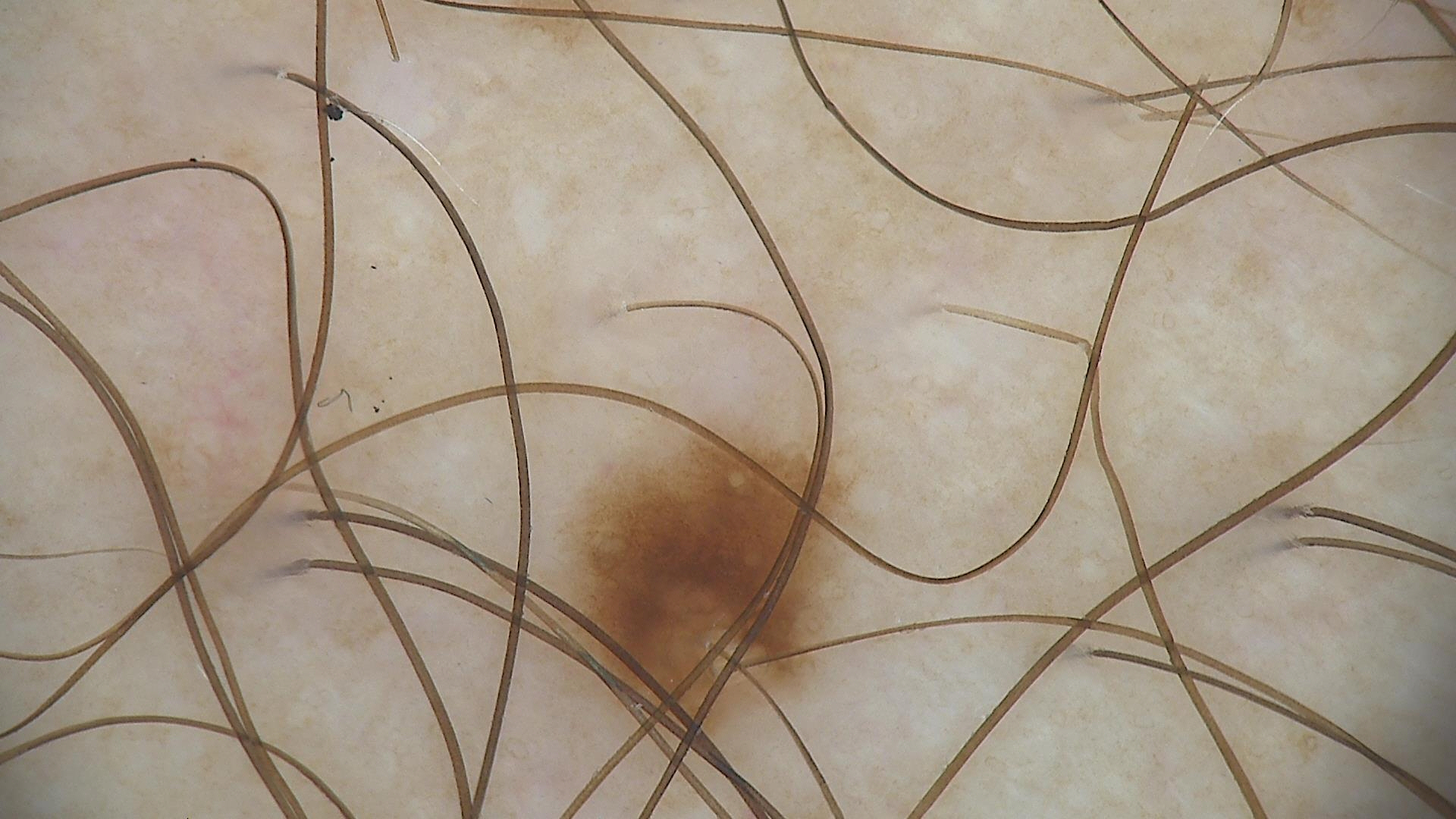class = junctional nevus (expert consensus)